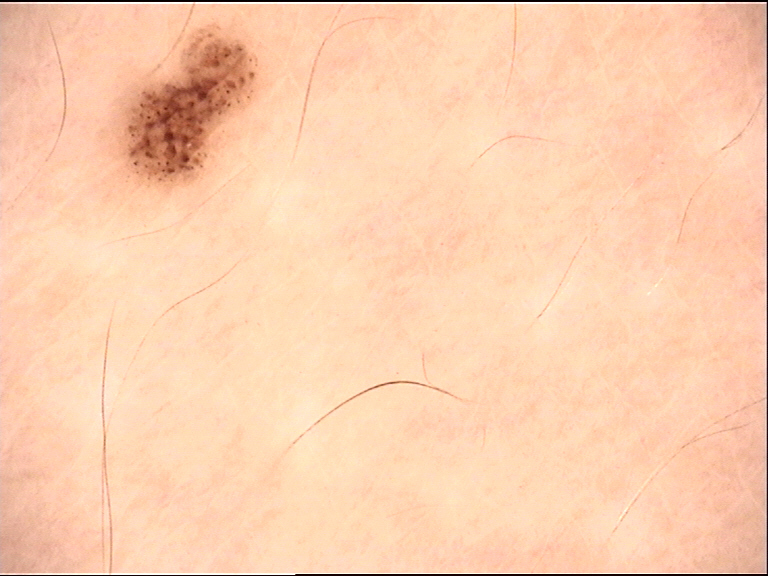Dermoscopy of a skin lesion.
Labeled as a banal lesion — a junctional nevus.